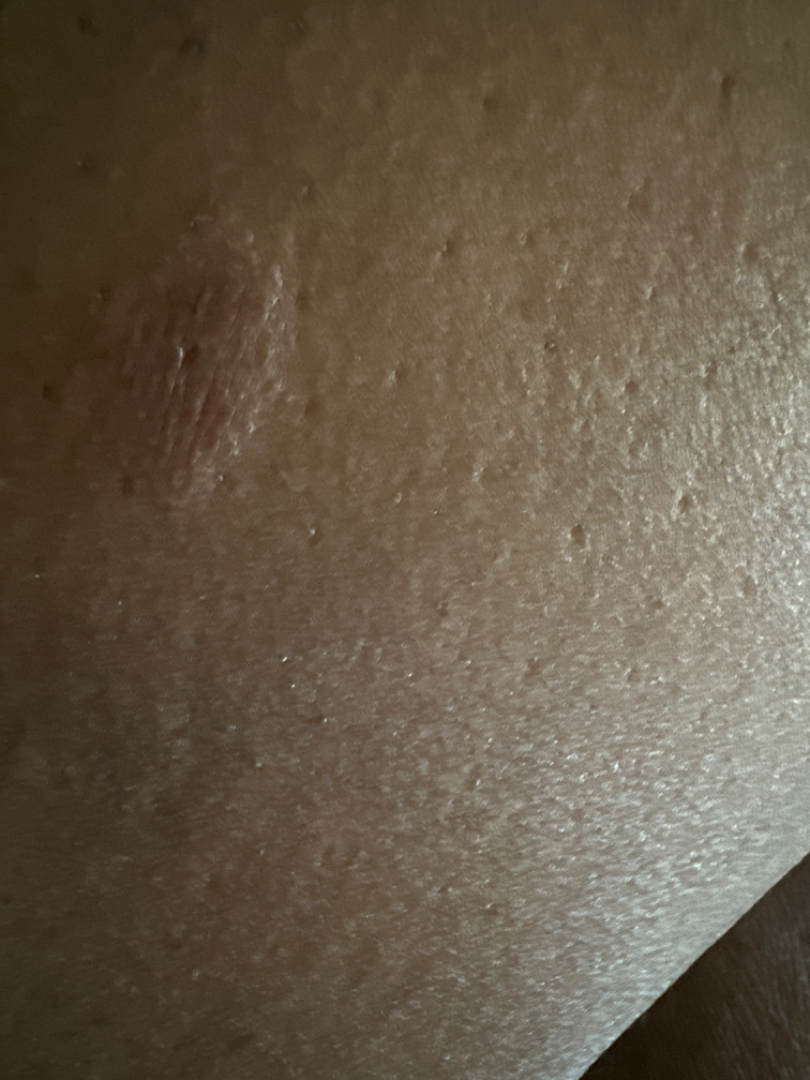| field | value |
|---|---|
| assessment | indeterminate from the photograph |